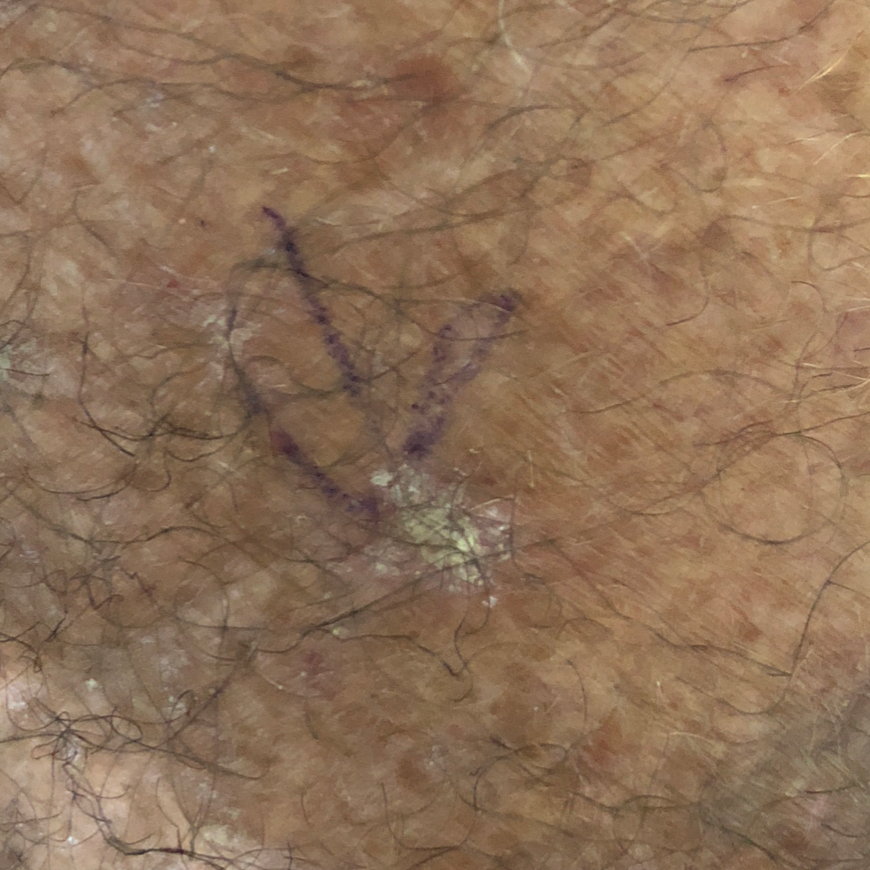The lesion is on a forearm. Expert review favored an actinic keratosis.